The photograph is a close-up of the affected area. The affected area is the leg: 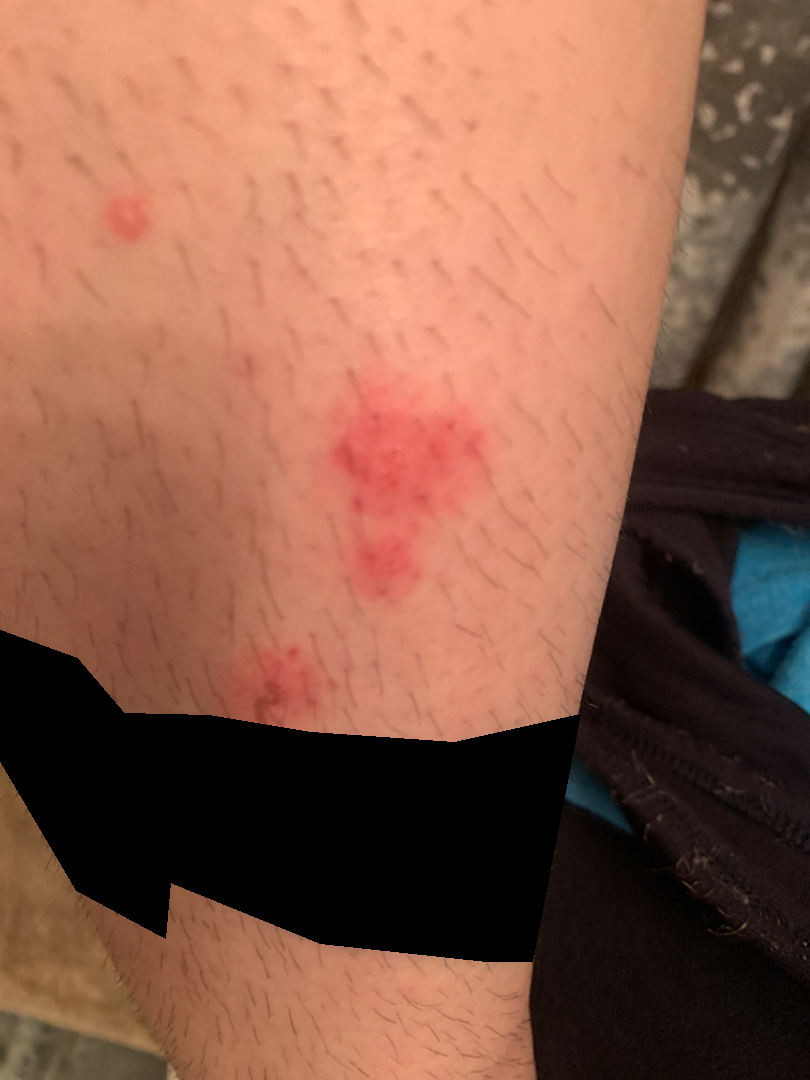The image was not sufficient for the reviewer to characterize the skin condition.